The subject is a male aged 68-72. A dermoscopic close-up of a skin lesion.
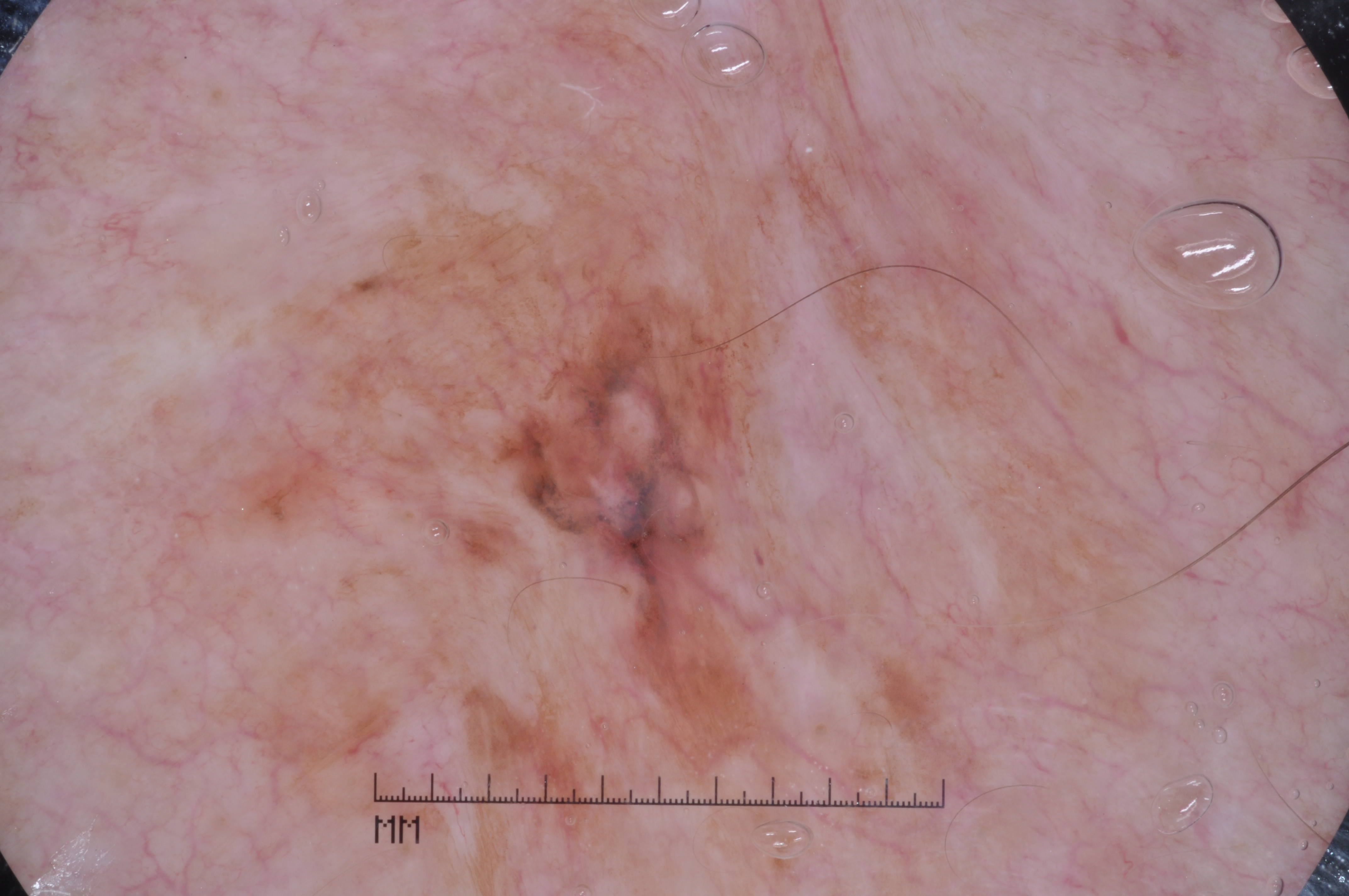Notes:
– lesion location: x1=109, y1=12, x2=1227, y2=892
– dermoscopic features assessed but absent: milia-like cysts, pigment network, streaks, and negative network
– diagnostic label: a melanoma, a malignancy